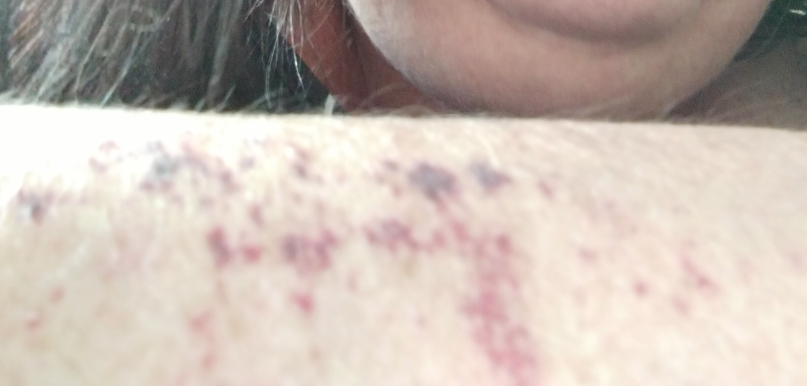Findings:
• assessment · not assessable
• history · one to four weeks
• reported symptoms · bothersome appearance and itching
• affected area · arm
• described texture · flat
• view · at a distance